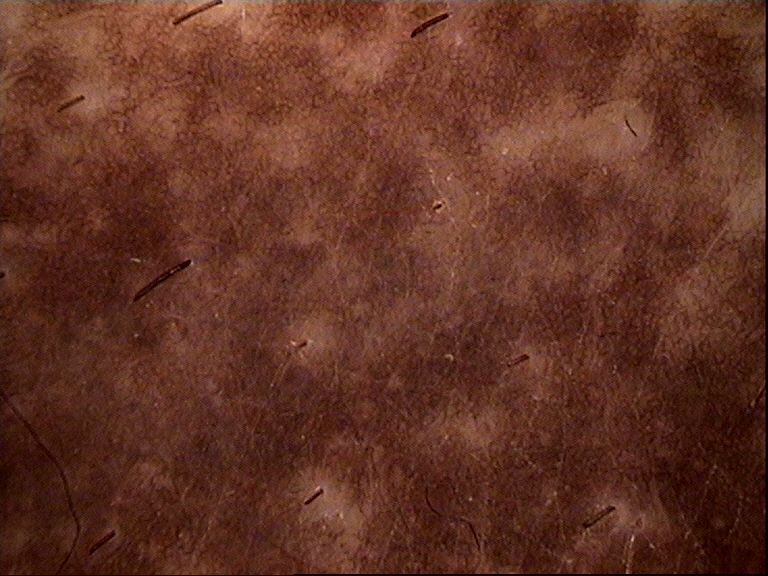diagnostic label: congenital compound nevus (expert consensus).